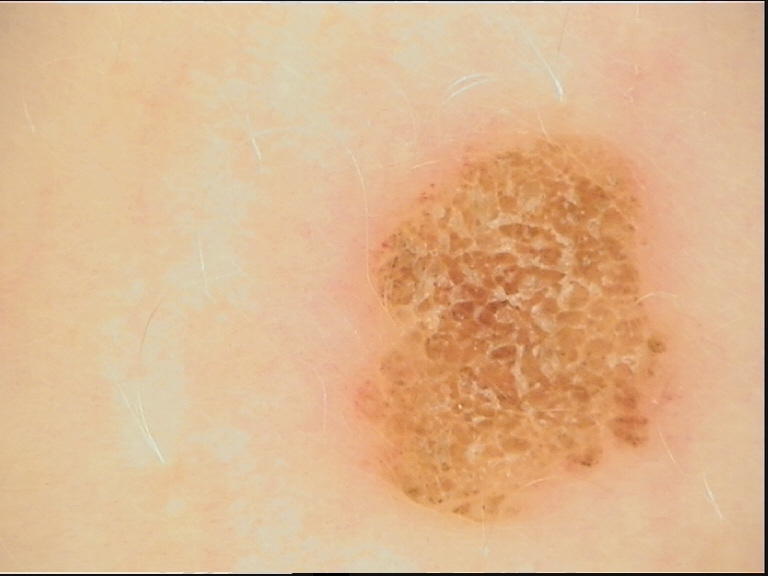Q: What is the diagnosis?
A: compound nevus (expert consensus)